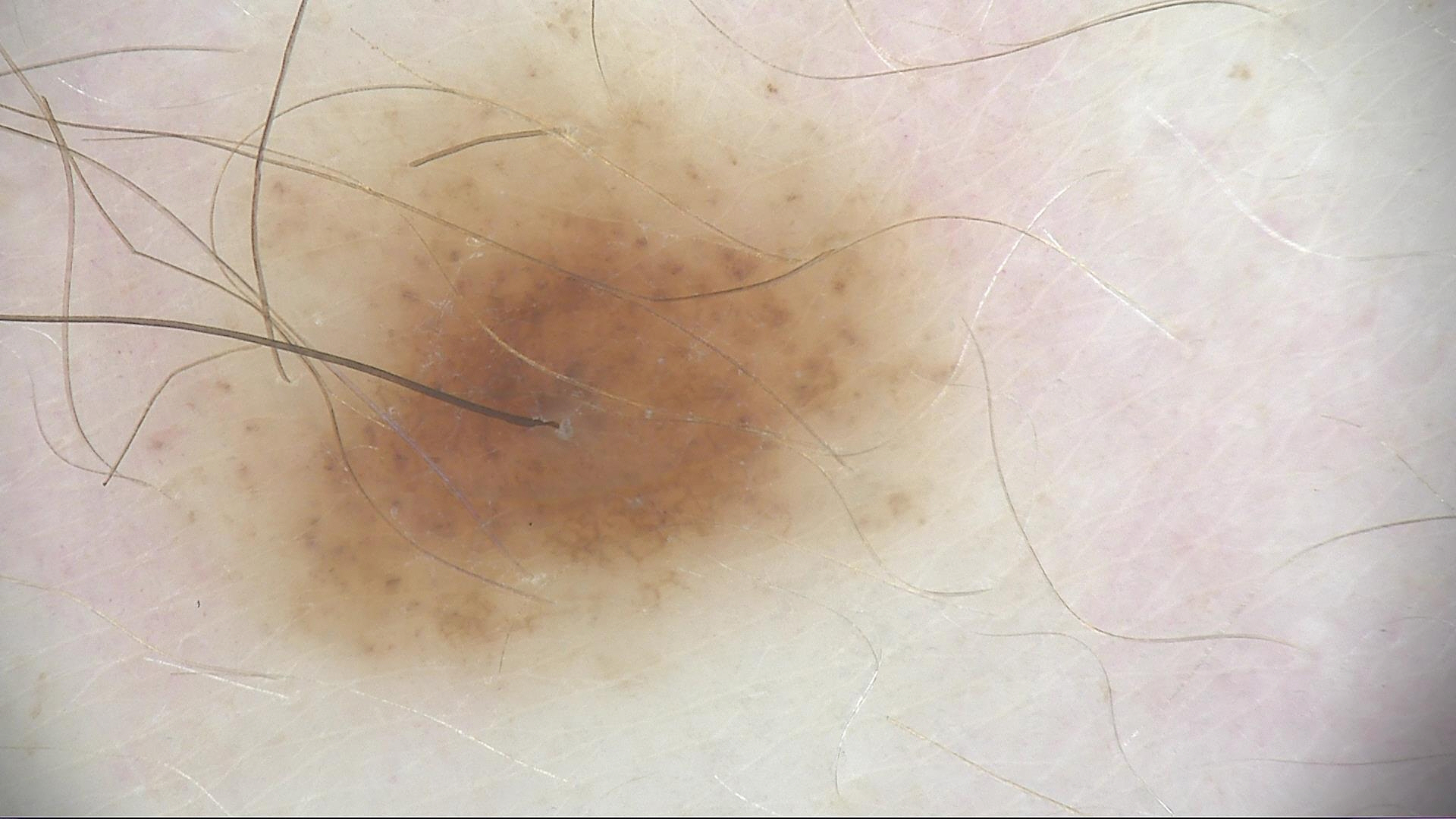Case:
A skin lesion imaged with a dermatoscope.
Impression:
Labeled as a banal lesion — a compound nevus.